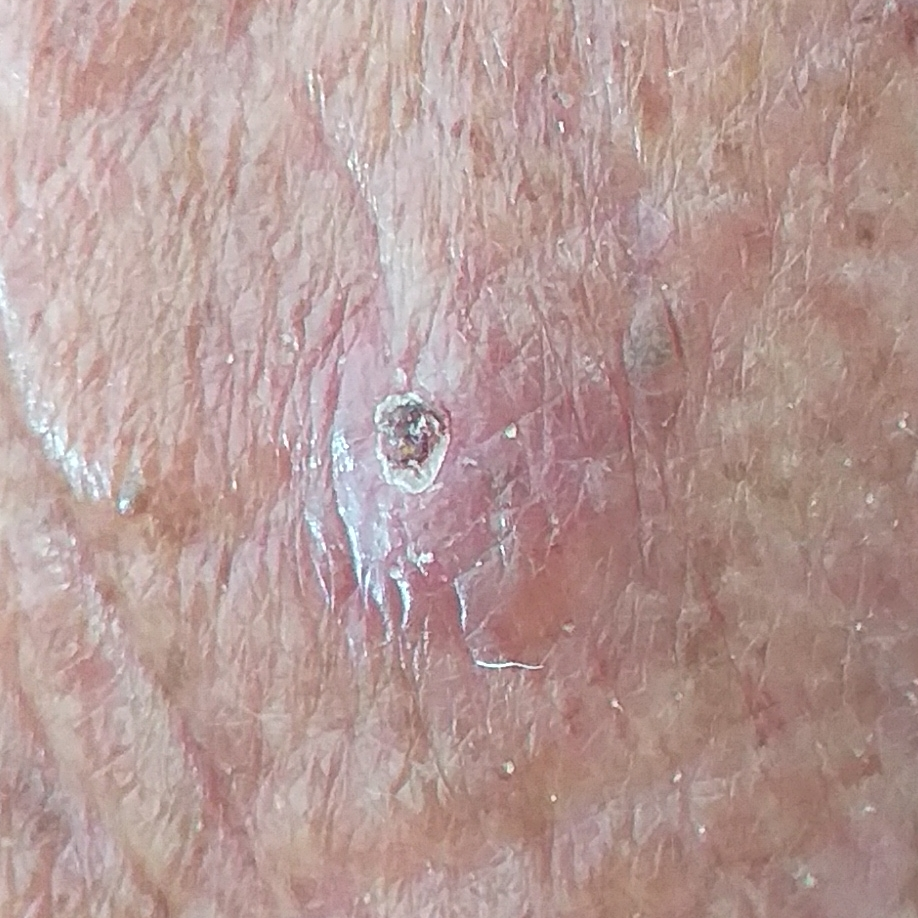Q: Skin phototype?
A: II
Q: What is the anatomic site?
A: the neck
Q: How large is the lesion?
A: 7x4 mm
Q: Any reported symptoms?
A: itching, elevation
Q: What is the diagnosis?
A: squamous cell carcinoma (biopsy-proven)